An image taken at a distance · female contributor, age 18–29 · the lesion involves the leg.
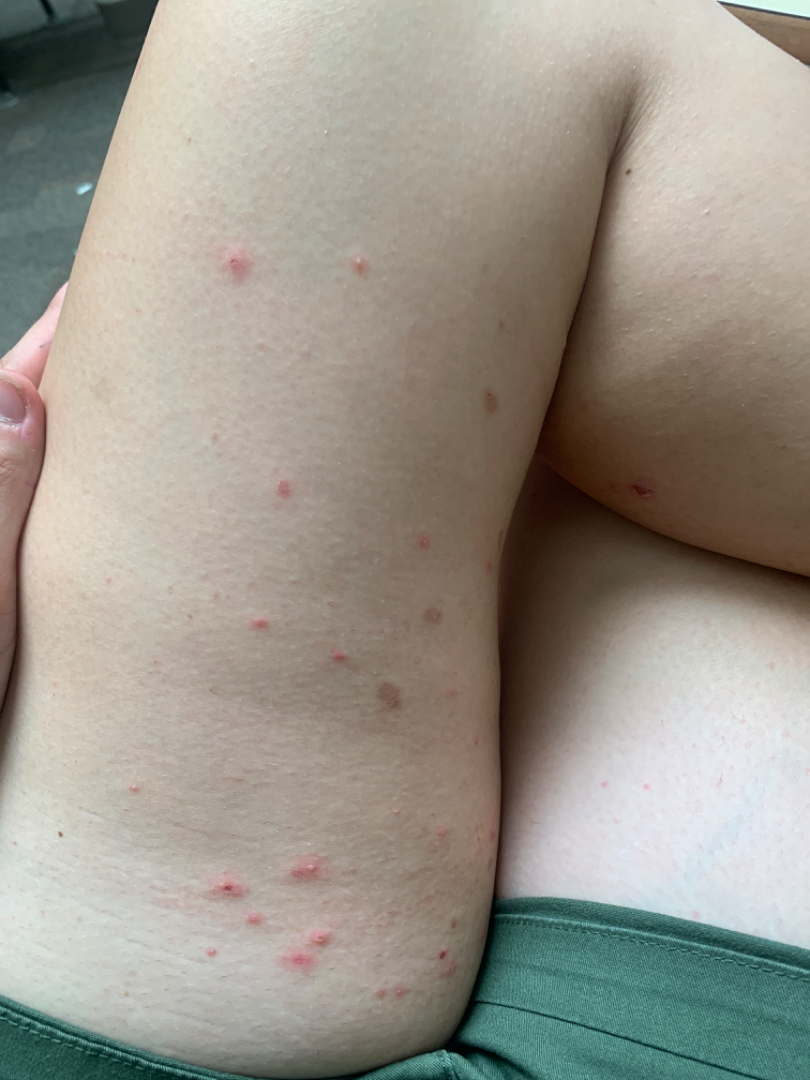| key | value |
|---|---|
| diagnostic considerations | the reviewer's impression was Folliculitis |